The patient described the issue as a rash · the patient also reports fatigue, joint pain and chills · the photo was captured at an angle · the lesion is described as raised or bumpy · the patient indicates the condition has been present for less than one week · symptoms reported: burning, itching and pain.
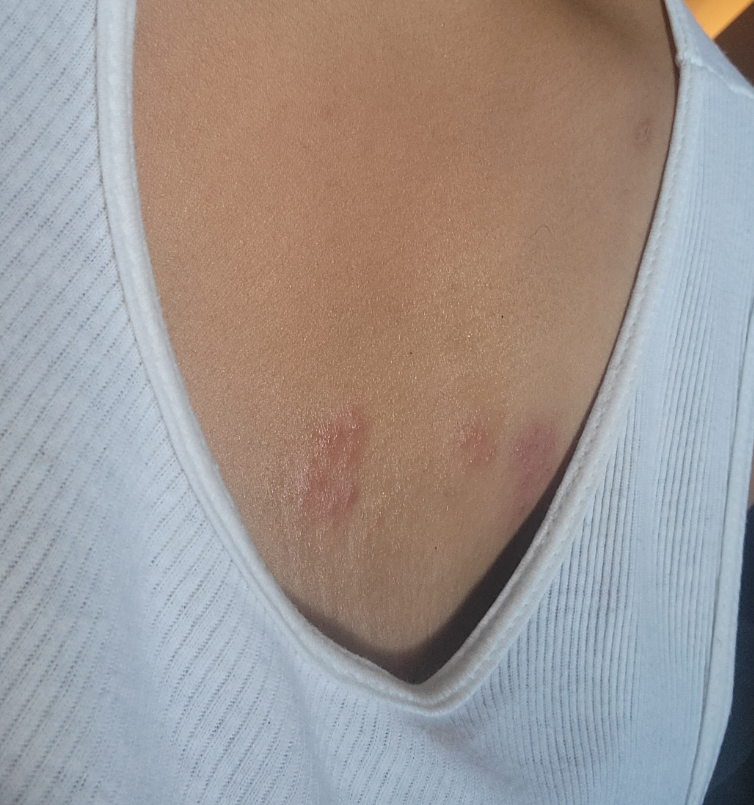differential diagnosis = the leading consideration is Herpes Zoster; less likely is Contact dermatitis; less probable is Allergic Contact Dermatitis; lower on the differential is Herpes Simplex.